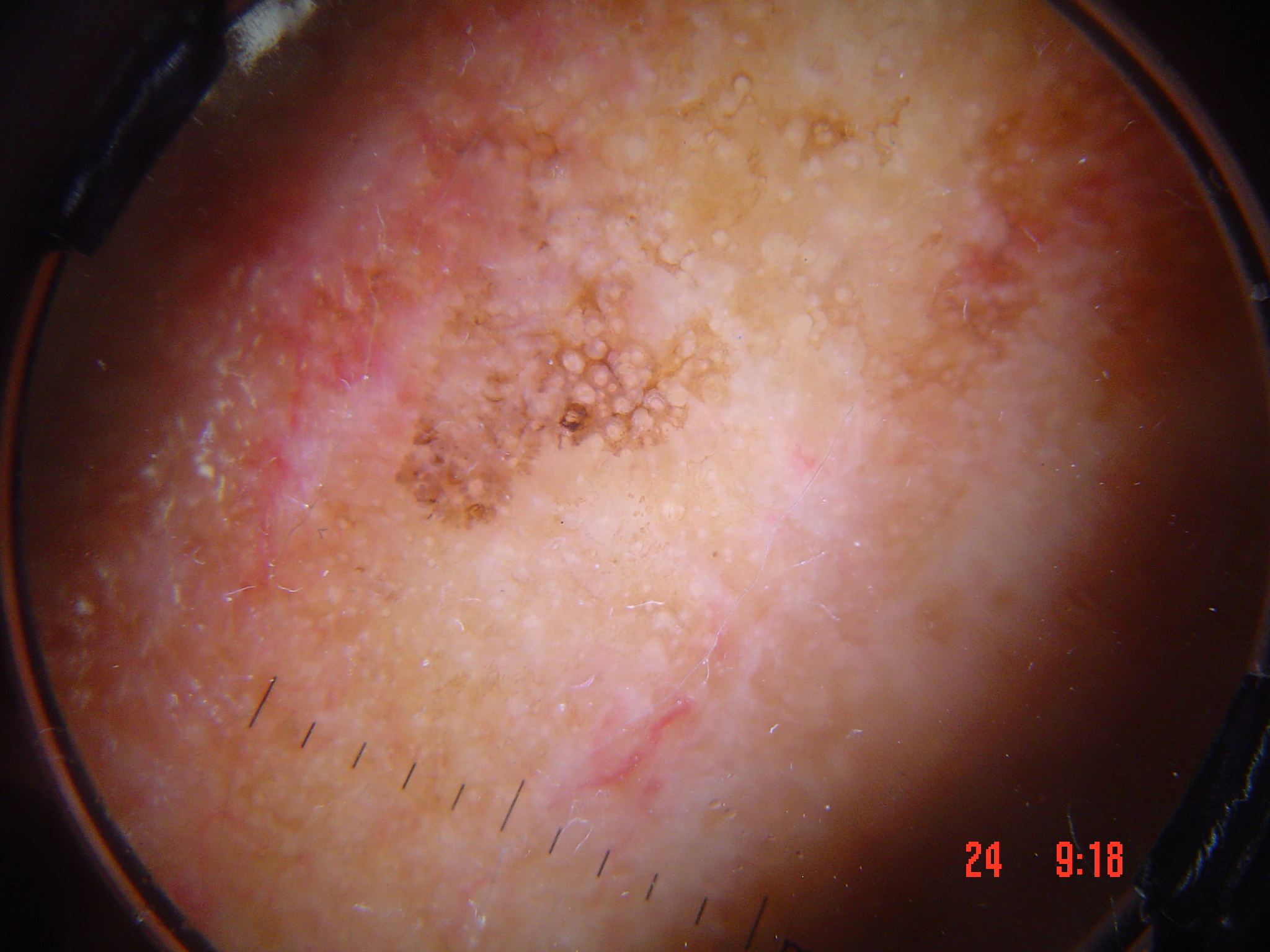<dermoscopy>
  <diagnosis>
    <name>actinic keratosis</name>
    <code>ak</code>
    <malignancy>indeterminate</malignancy>
    <super_class>non-melanocytic</super_class>
    <confirmation>expert consensus</confirmation>
  </diagnosis>
</dermoscopy>